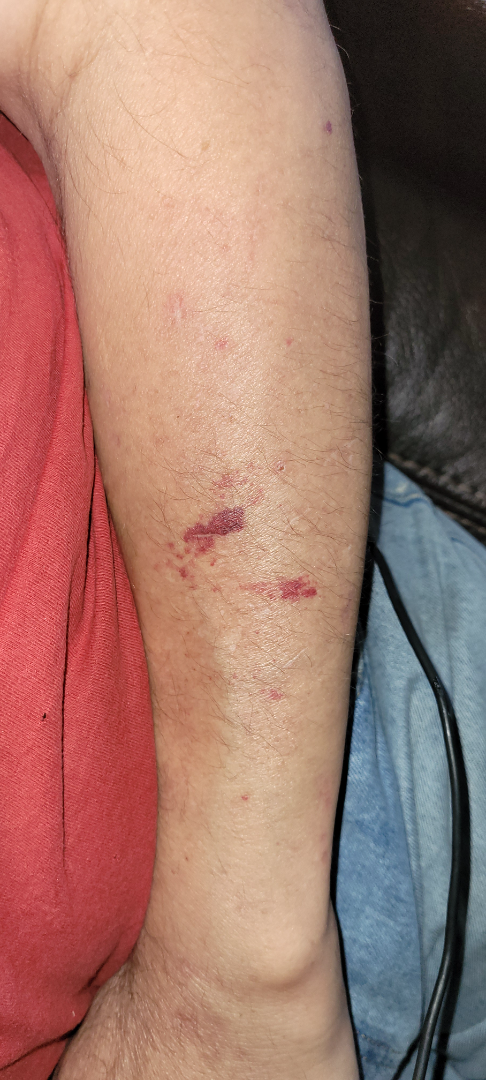Male contributor, age 50–59. The arm is involved. Reported duration is about one day. The photo was captured at a distance. Symptoms reported: bothersome appearance. Texture is reported as raised or bumpy. The patient described the issue as a rash. The patient reports associated joint pain. On teledermatology review, the reviewer's impression was ecchymoses.